This image was taken at an angle:
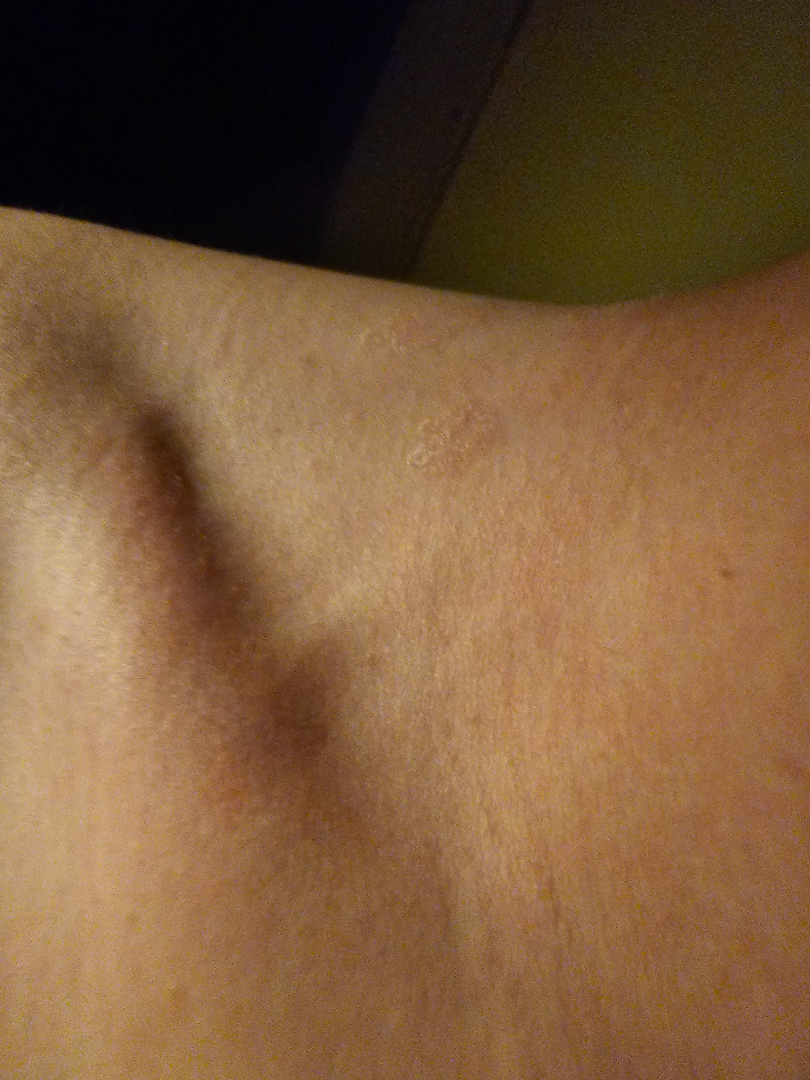A single dermatologist reviewed the case: the differential is split between Pityriasis rosea, Tinea Versicolor and Seborrheic Dermatitis.